A dermoscopic close-up of a skin lesion. The patient was assessed as Fitzpatrick II.
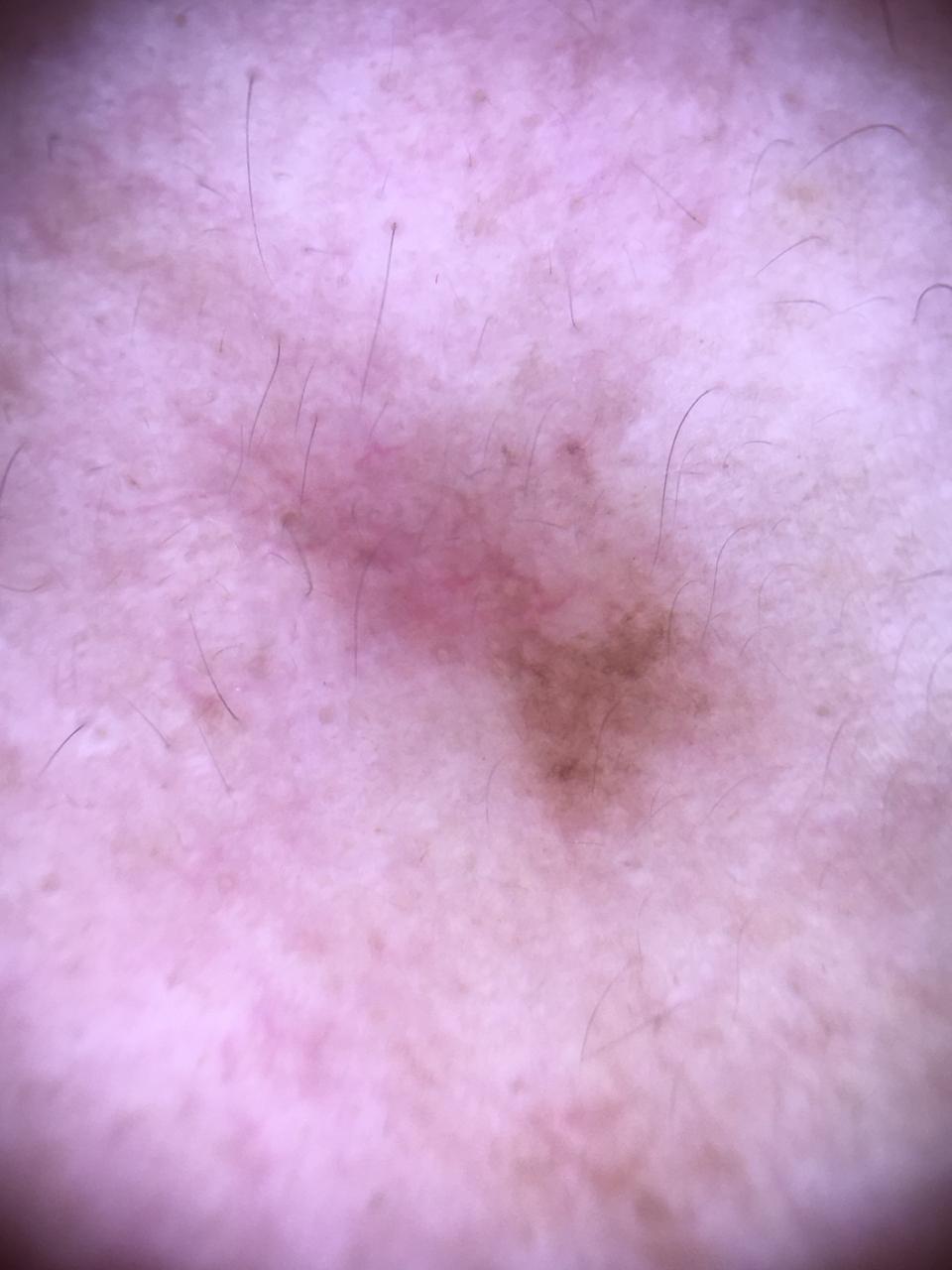anatomic site: the head or neck, diagnosis: Melanoma (biopsy-proven).